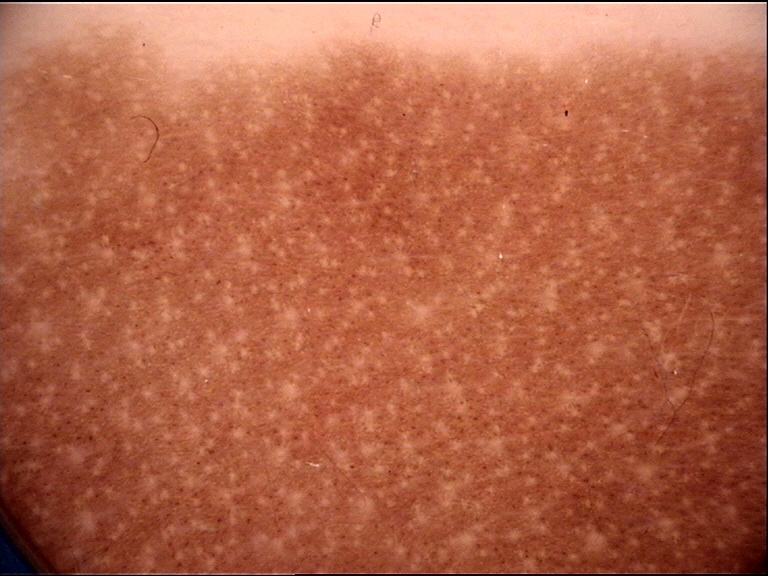Impression: Classified as a congenital compound nevus.